A skin lesion imaged with a dermatoscope:
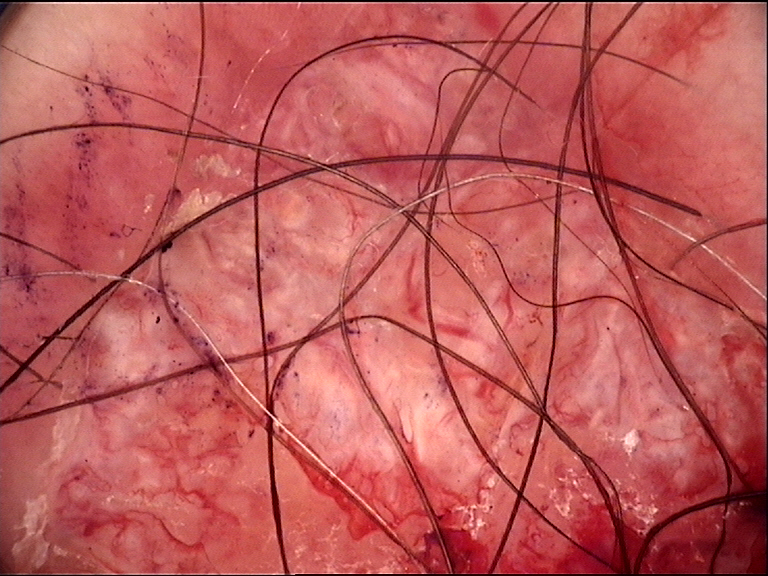lesion_type:
  main_class: keratinocytic
diagnosis:
  name: basal cell carcinoma
  code: bcc
  malignancy: malignant
  super_class: non-melanocytic
  confirmation: histopathology